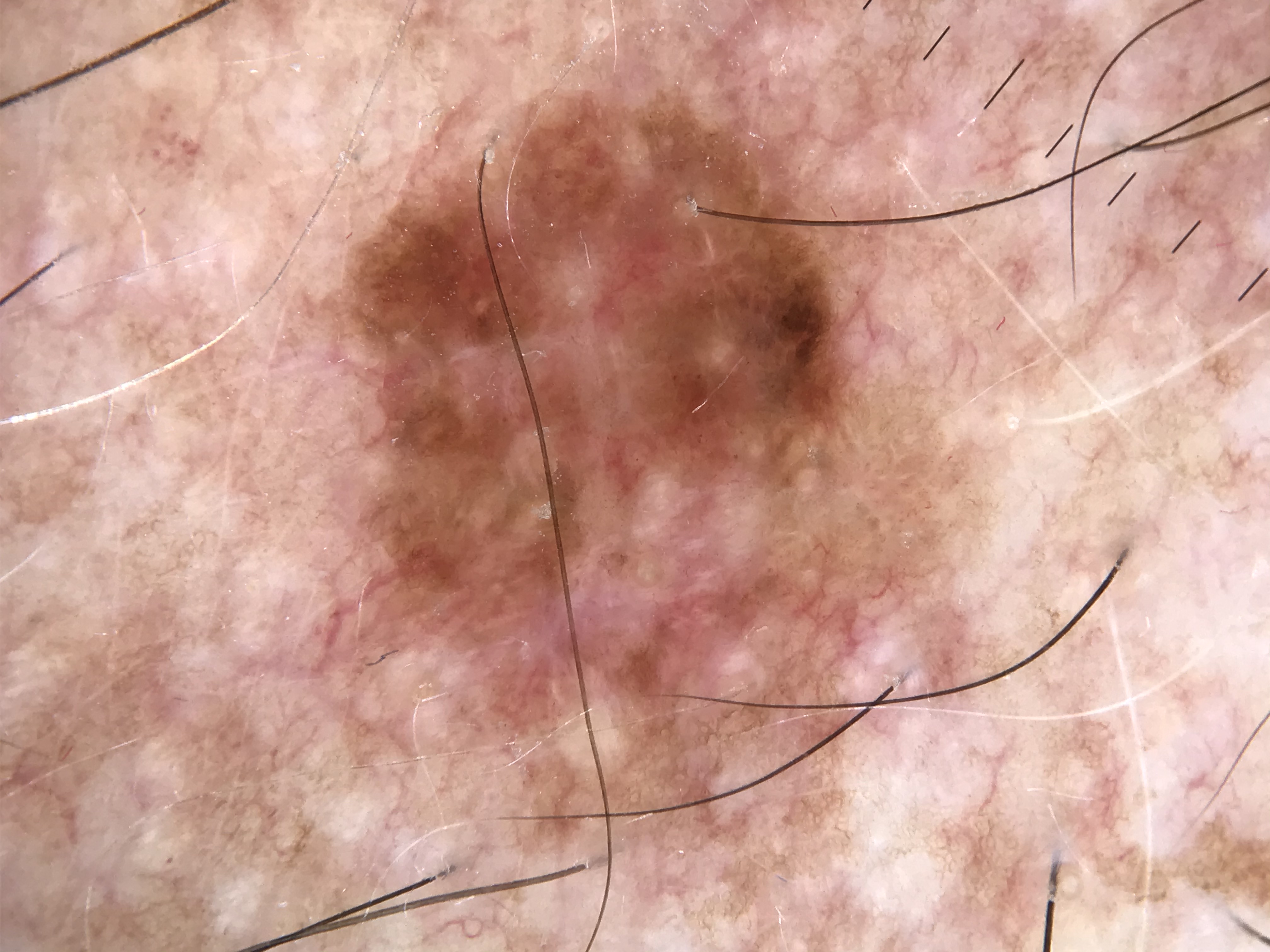image = dermoscopy; diagnostic label = melanoma (biopsy-proven).